A dermatoscopic image of a skin lesion.
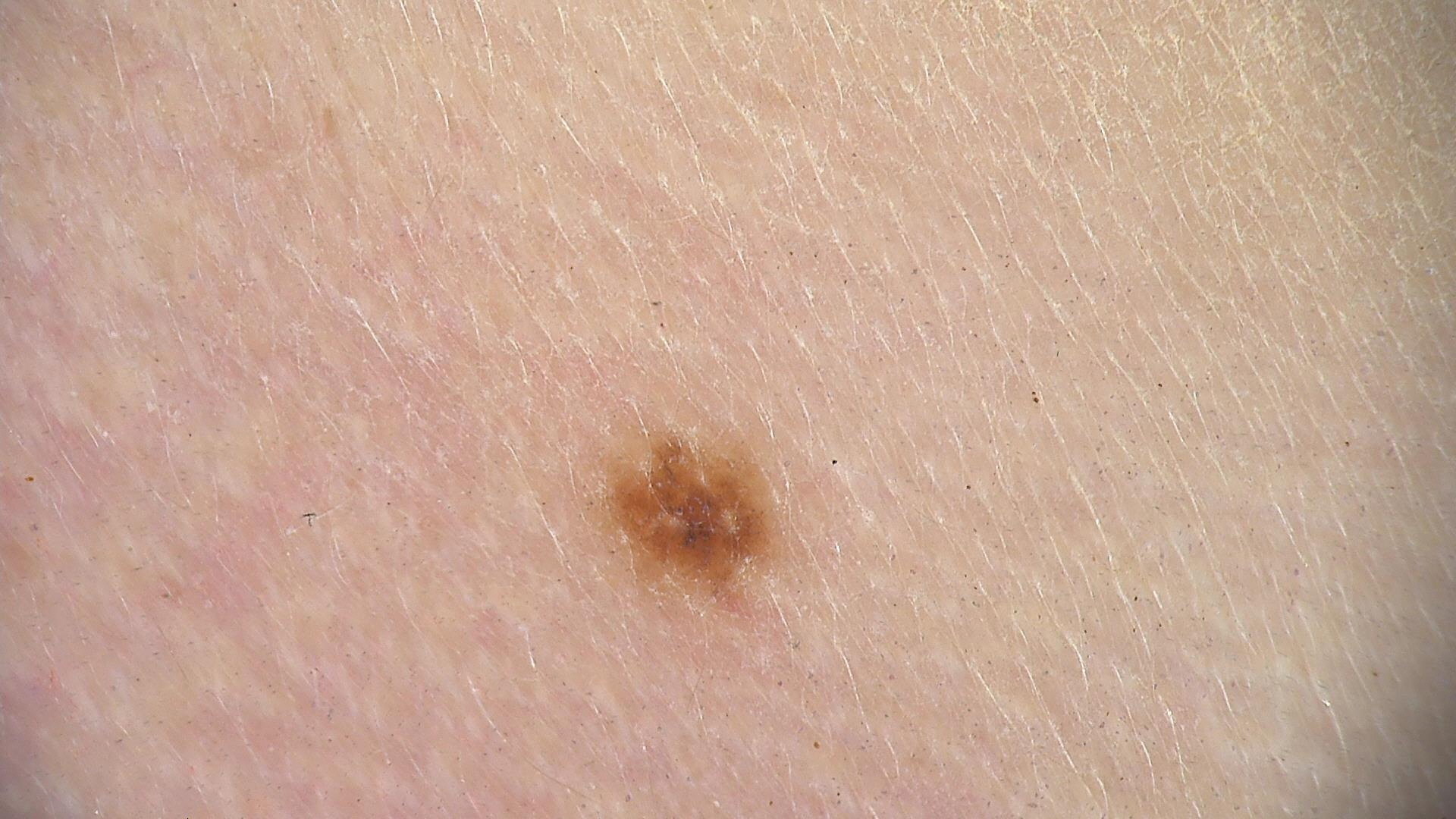The diagnostic label was a benign lesion — a dysplastic junctional nevus.